A skin lesion imaged with a dermatoscope.
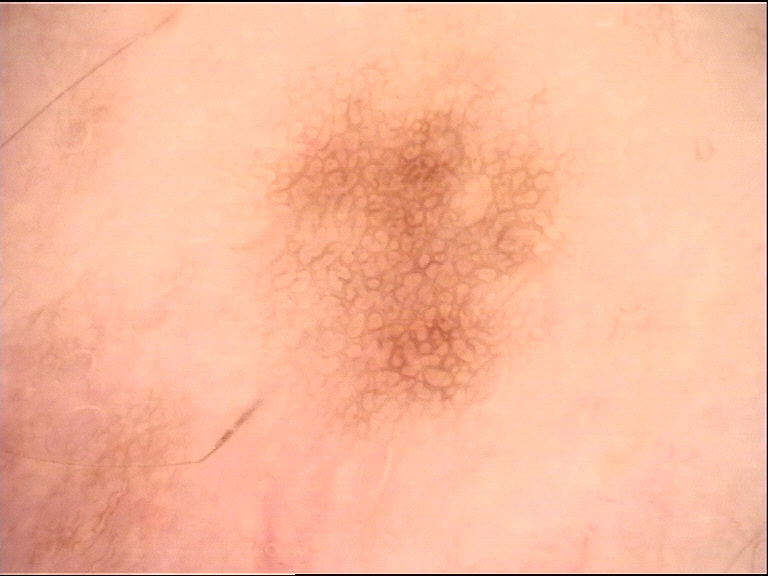Diagnosed as a benign lesion — a dysplastic junctional nevus.